The contributor is 40–49, female; this is a close-up image; the leg is involved — 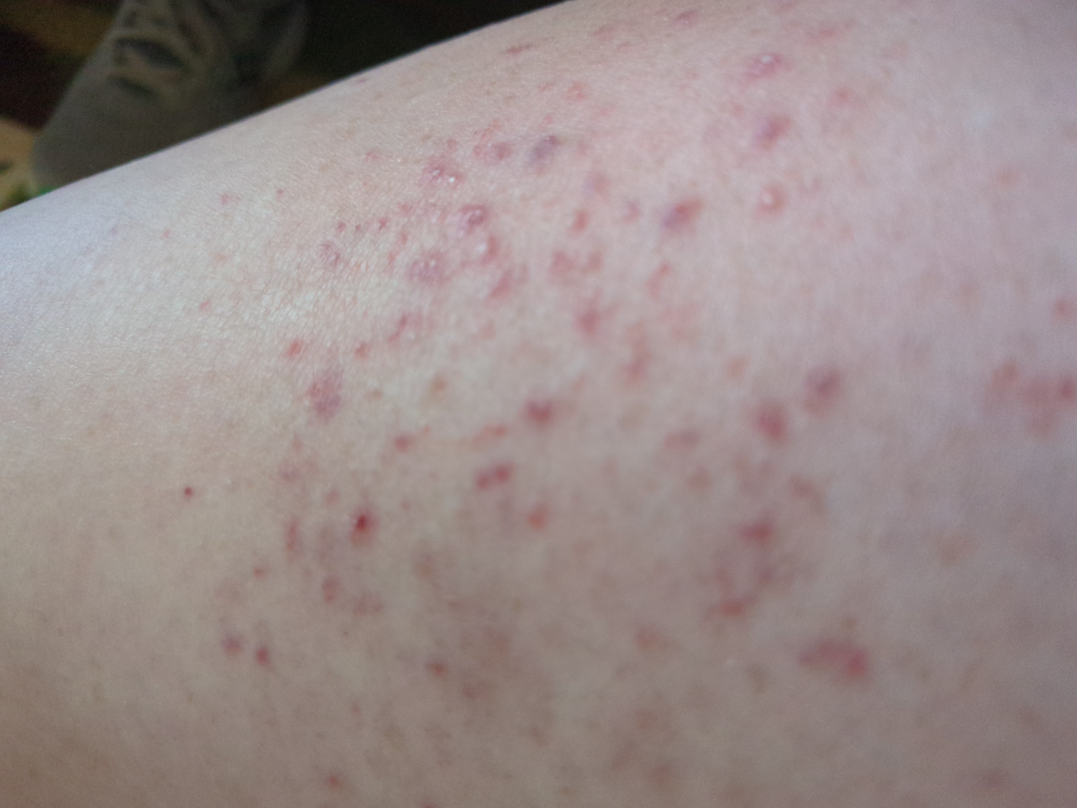The patient considered this a rash.
The condition has been present for less than one week.
Symptoms reported: itching, pain, bothersome appearance, burning and enlargement.
No associated systemic symptoms reported.
On remote dermatologist review, favoring Leukocytoclastic Vasculitis.